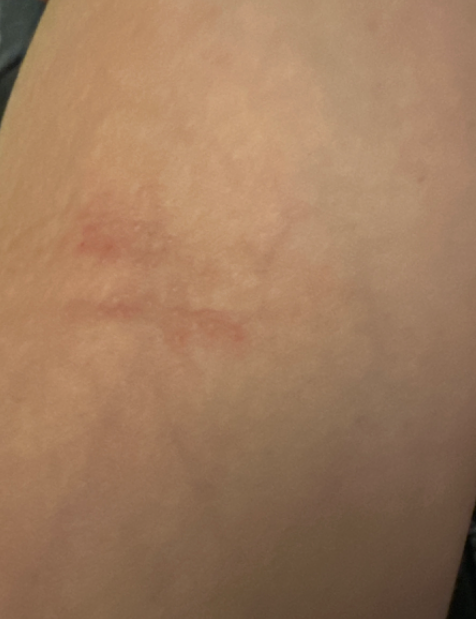Background: The patient indicates the condition has been present for less than one week. The lesion is associated with itching. The arm is involved. No relevant systemic symptoms. The photo was captured at an angle. The patient described the issue as a rash. The contributor is a female aged 18–29. Texture is reported as fluid-filled and raised or bumpy. Findings: The leading impression is Eczema; with consideration of Tinea; also consider Allergic Contact Dermatitis.